History notes prior skin cancer (patient or family) and no pesticide exposure. A clinical close-up photograph of a skin lesion: 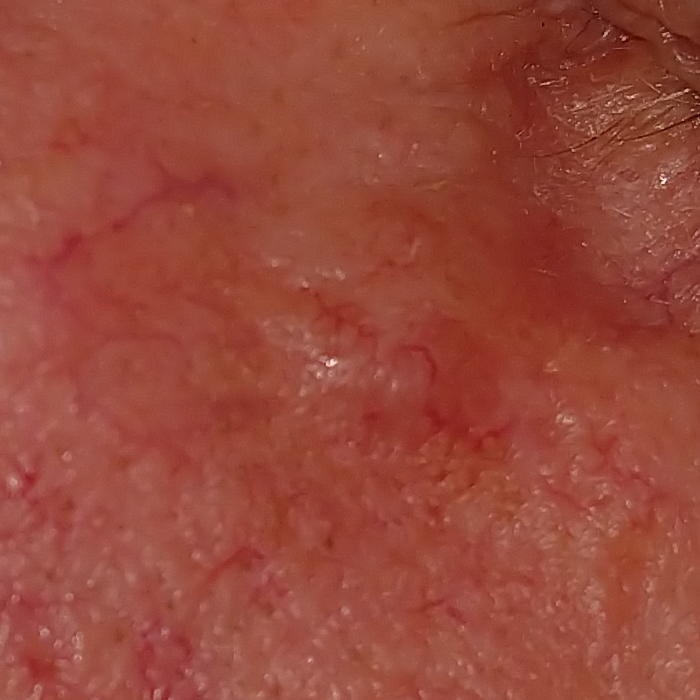The patient describes that the lesion has grown, but has not changed and has not bled. Biopsy-confirmed as a basal cell carcinoma.